The photo was captured at an angle.
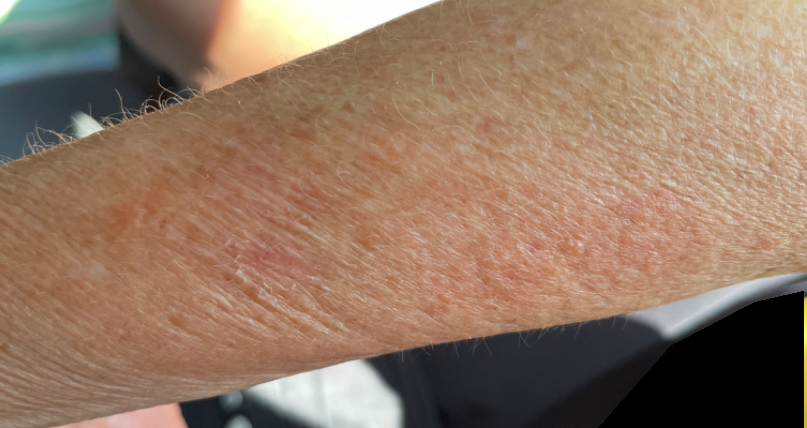Diagnostic features were not clearly distinguishable in this photograph.
The condition has been present for one to four weeks.
Reported lesion symptoms include itching and enlargement.
The patient considered this a rash.
The lesion is described as raised or bumpy.